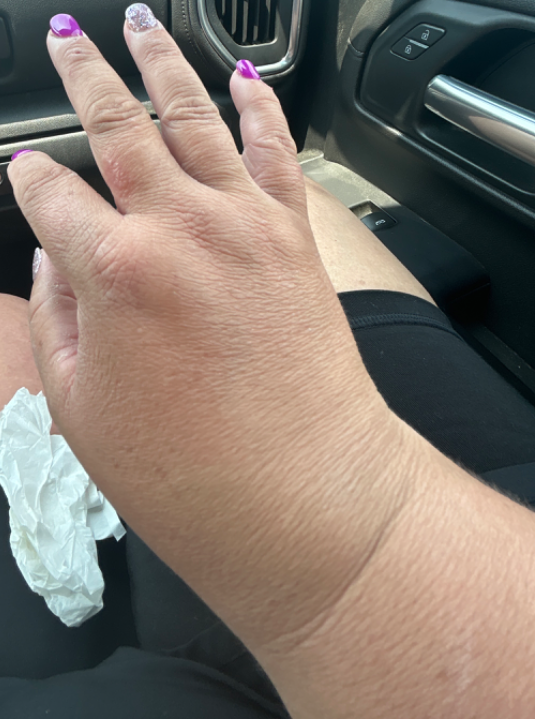The skin findings could not be characterized from the image.
The lesion is associated with itching and pain.
This image was taken at a distance.